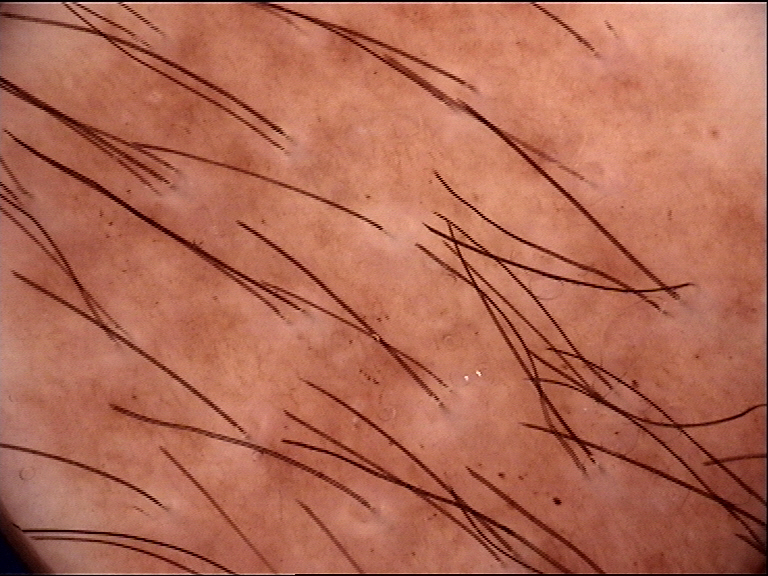classification = banal, class = congenital junctional nevus (expert consensus).